The contributor is 40–49, female · this is a close-up image · the lesion involves the leg, arm and head or neck:
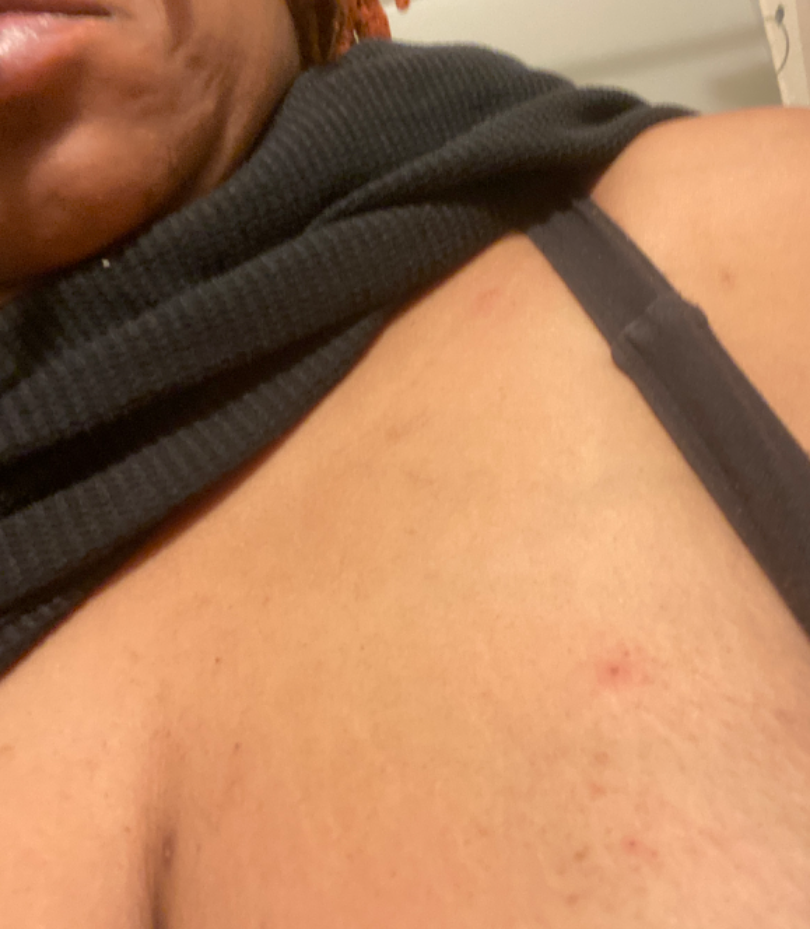Clinical context: Fitzpatrick V; lay reviewers estimated Monk skin tone scale 6 (US pool) or 3 (India pool). Reported lesion symptoms include itching. The patient reports the lesion is raised or bumpy. The condition has been present for less than one week. Assessment: On dermatologist assessment of the image: Acne and Folliculitis were each considered, in no particular order.